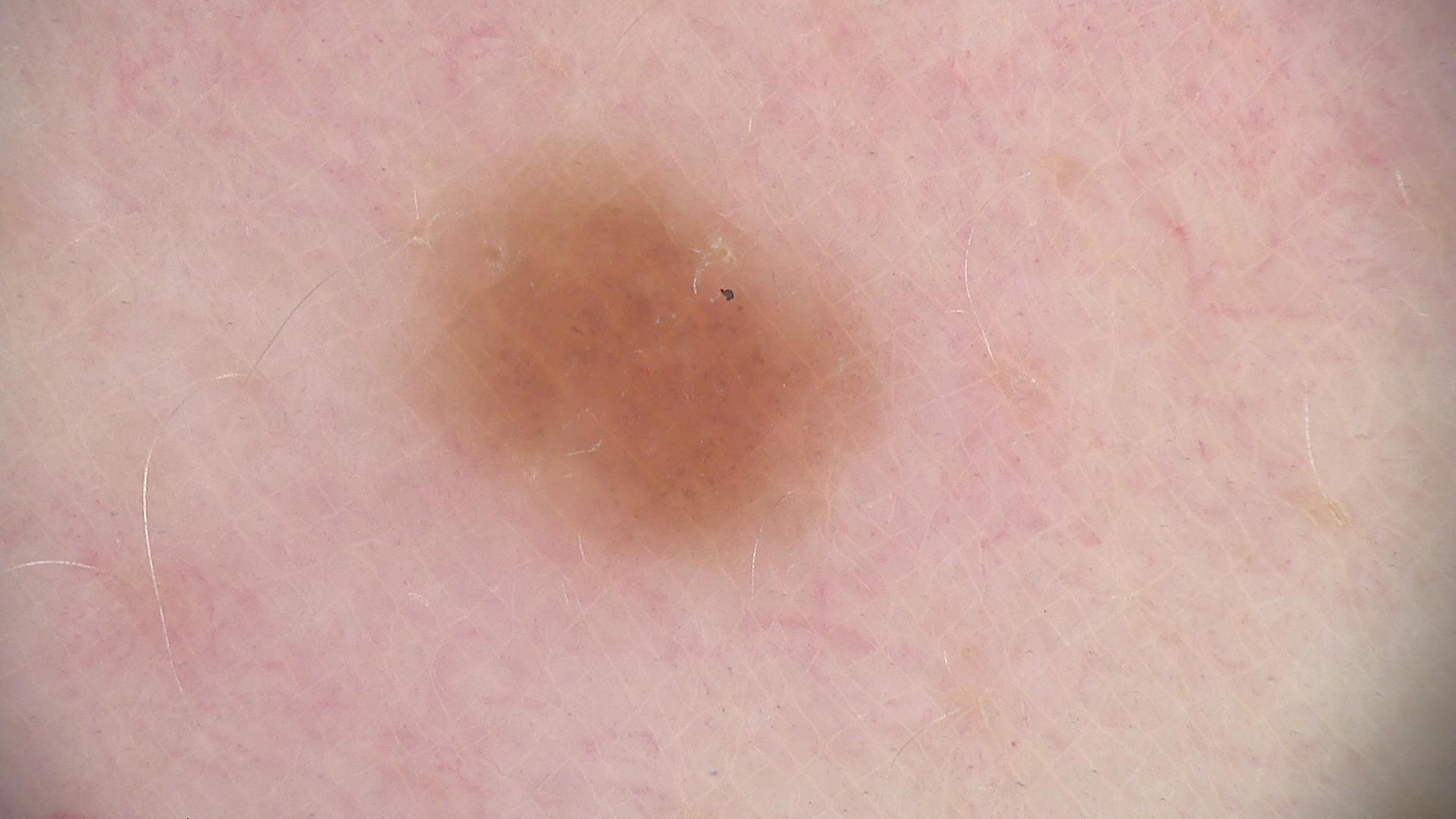assessment: dysplastic junctional nevus (expert consensus).